A dermoscopy image of a single skin lesion · Fitzpatrick II · a female subject aged around 40.
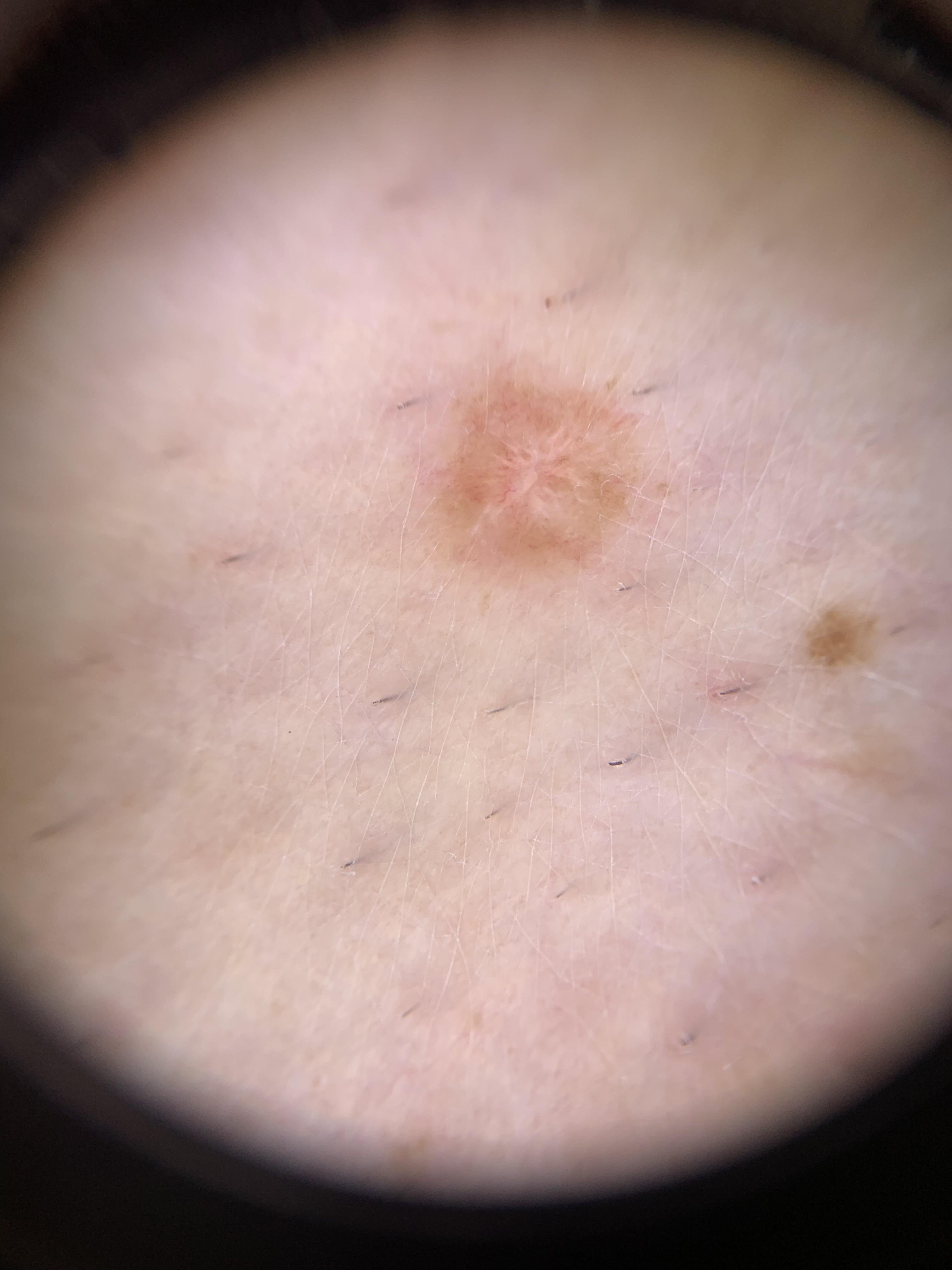| key | value |
|---|---|
| location | a lower extremity |
| diagnosis | Dermatofibroma (clinical impression) |